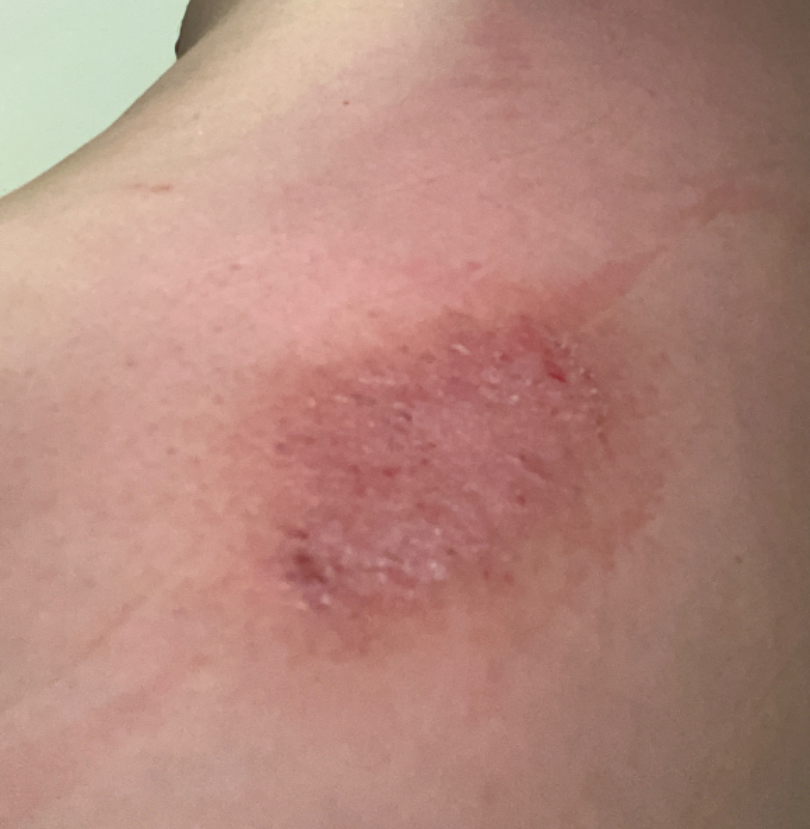Findings:
The case was indeterminate on photographic review.
Background:
Located on the back of the torso. No constitutional symptoms were reported. The contributor is male. Reported lesion symptoms include itching. The condition has been present for more than one year. The lesion is described as rough or flaky. Close-up view. Lay graders estimated MST 1 or 2 (two reviewer pools).